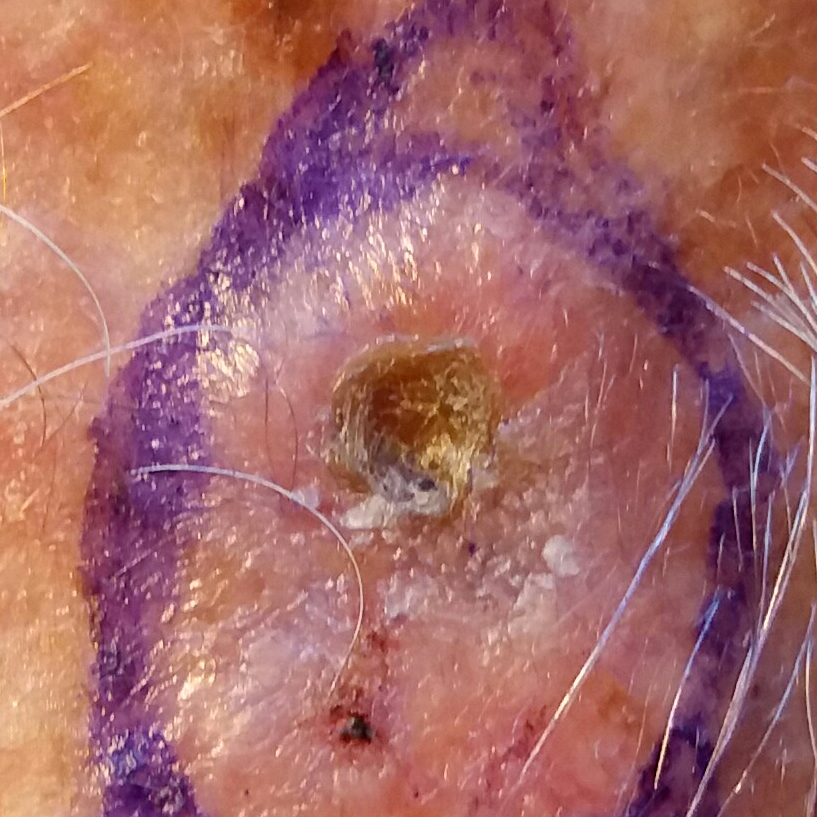<skin_lesion>
  <diagnosis>
    <name>squamous cell carcinoma</name>
    <code>SCC</code>
    <malignancy>malignant</malignancy>
    <confirmation>histopathology</confirmation>
  </diagnosis>
</skin_lesion>